The condition has been present for less than one week · symptoms reported: itching · the photo was captured at an angle · the subject is a female aged 50–59 · the leg is involved.
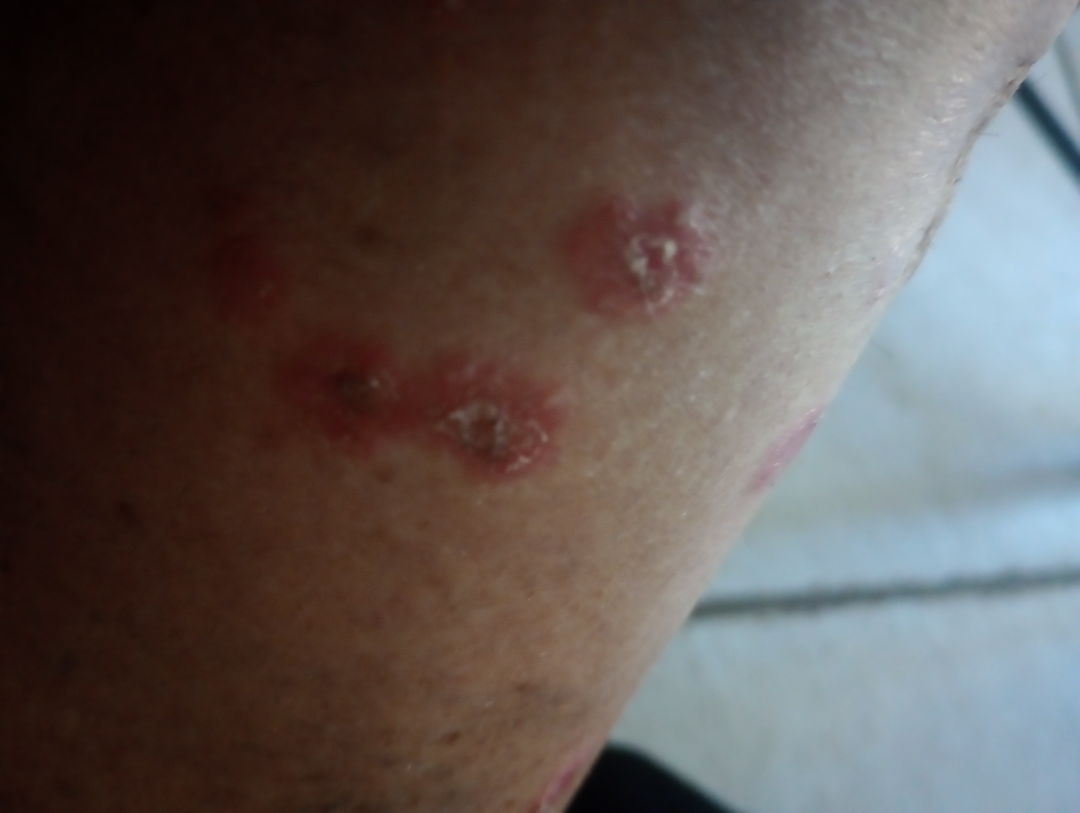Q: What was the assessment?
A: unable to determine